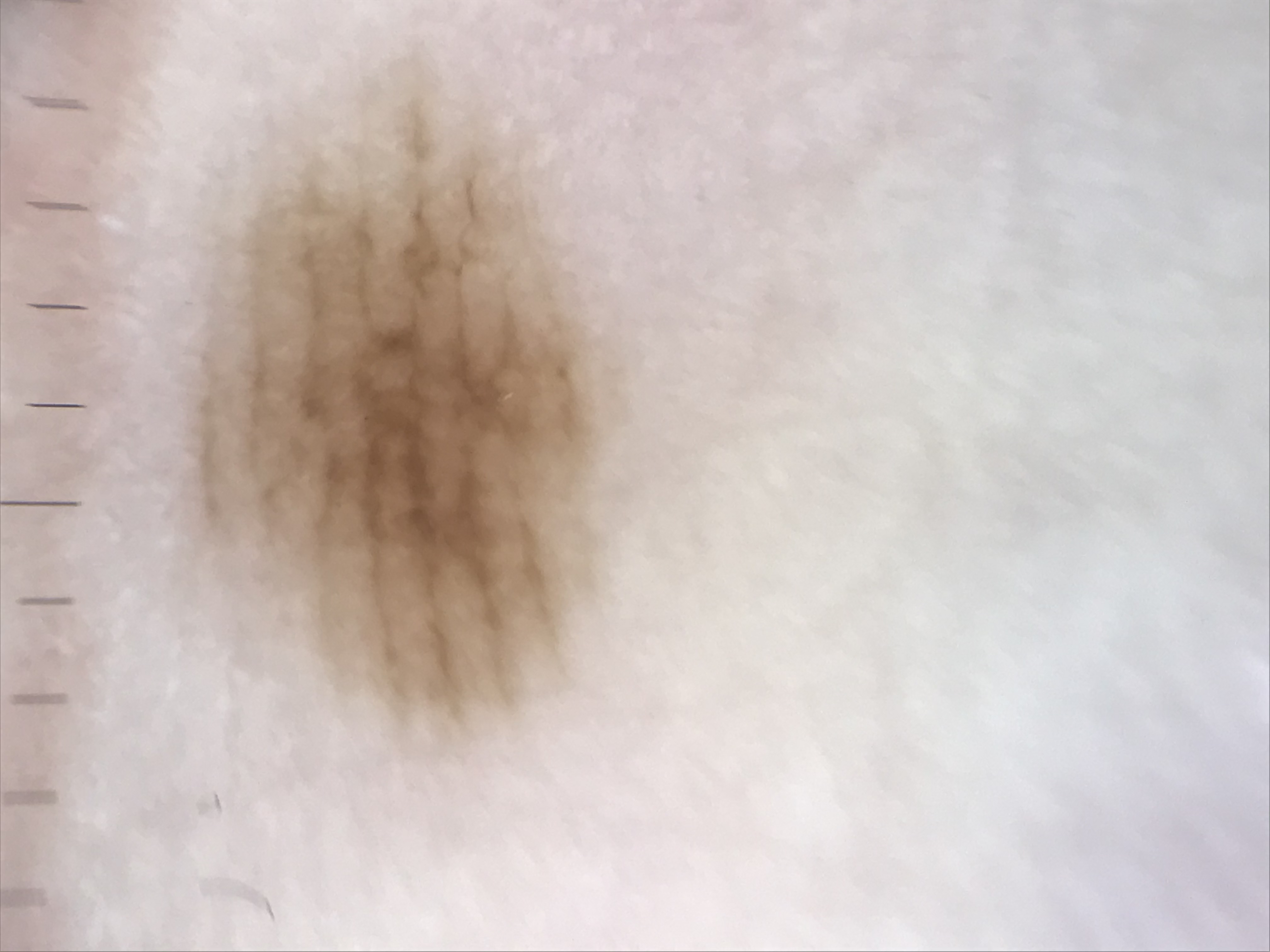{"lesion_type": {"main_class": "banal", "pattern": "junctional"}, "diagnosis": {"name": "acral junctional nevus", "code": "ajb", "malignancy": "benign", "super_class": "melanocytic", "confirmation": "expert consensus"}}